The patient reported no relevant symptoms from the lesion · the contributor notes the condition has been present for less than one week · this is a close-up image · the lesion involves the back of the hand · the patient described the issue as a rash · the lesion is described as raised or bumpy · female contributor, age 18–29.
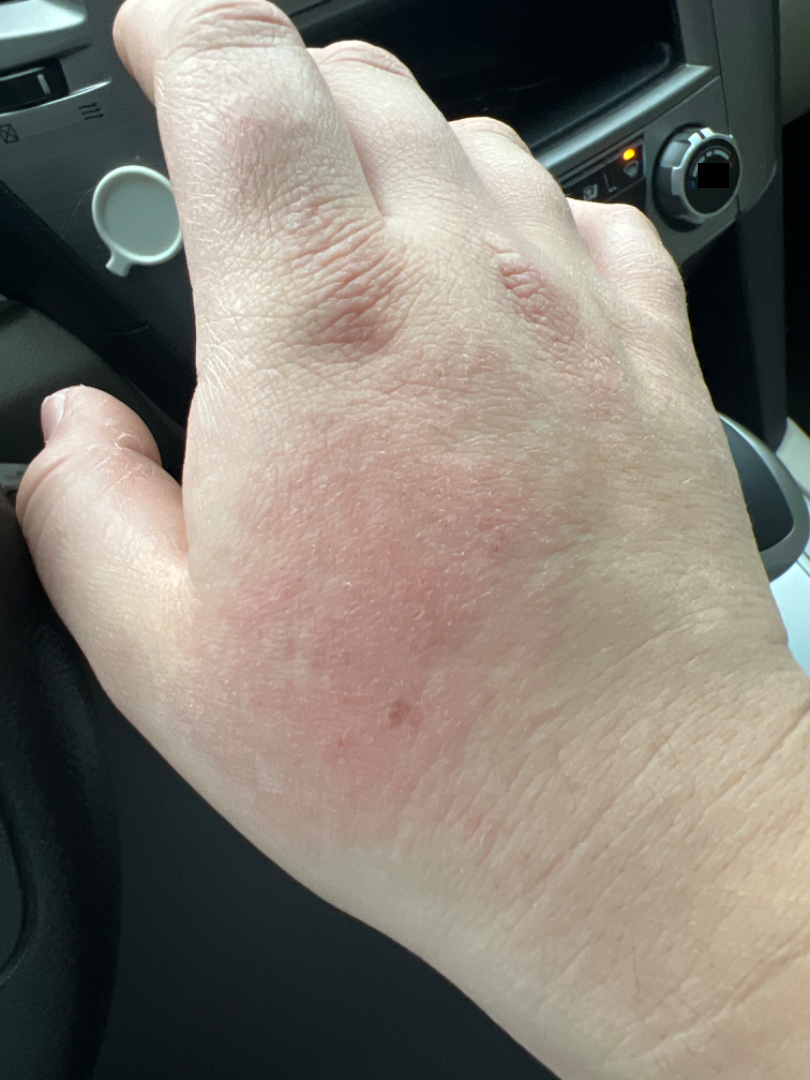Favoring Irritant Contact Dermatitis; also raised was Allergic Contact Dermatitis.